Texture is reported as raised or bumpy. A close-up photograph. The patient indicates itching. The patient indicates the condition has been present for less than one week. The patient described the issue as a rash — 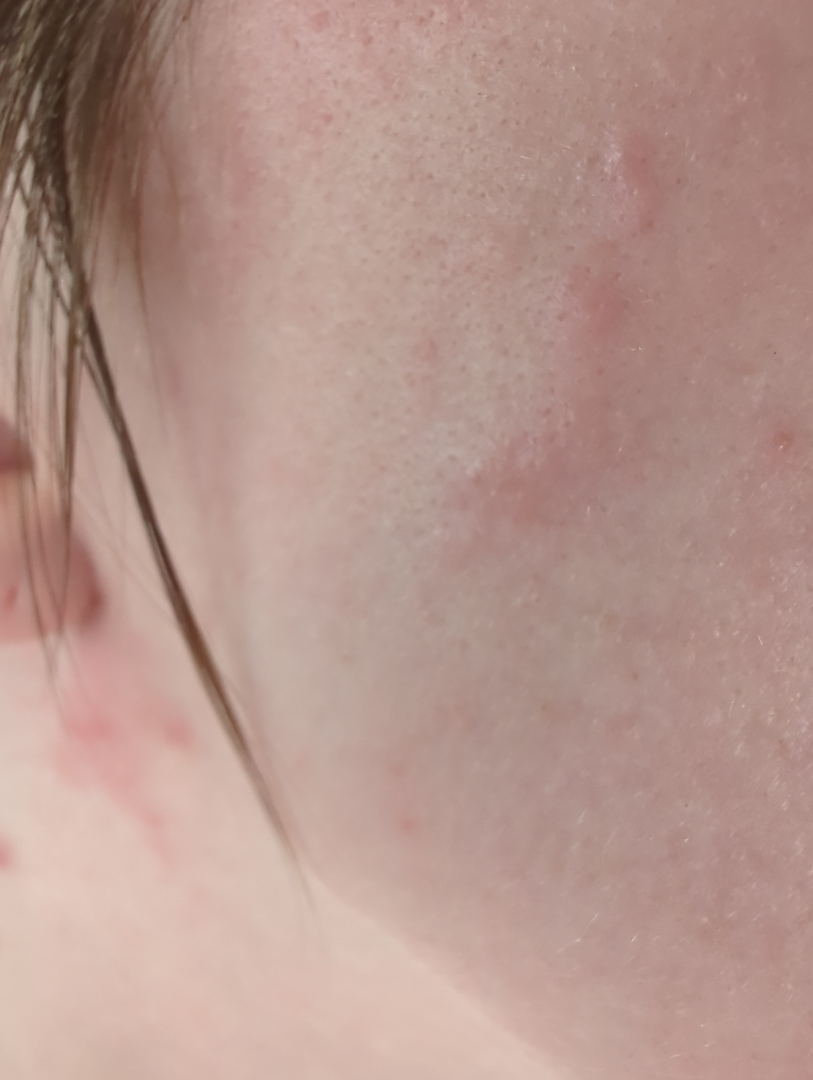On teledermatology review: the leading impression is Acne; with consideration of Rosacea; also raised was Allergic Contact Dermatitis.